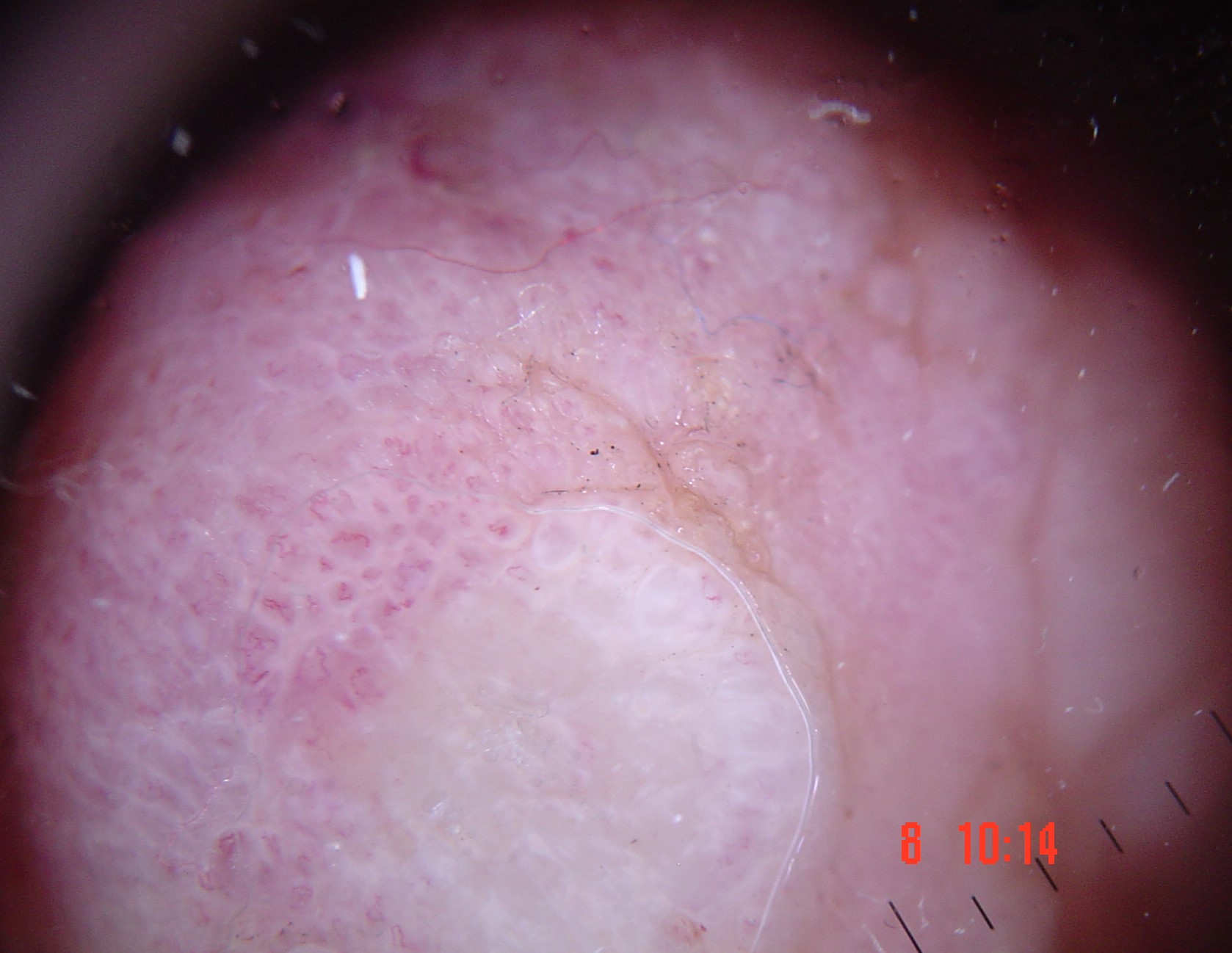A dermoscopic photograph of a skin lesion. Histopathology confirmed an acral nodular melanoma.